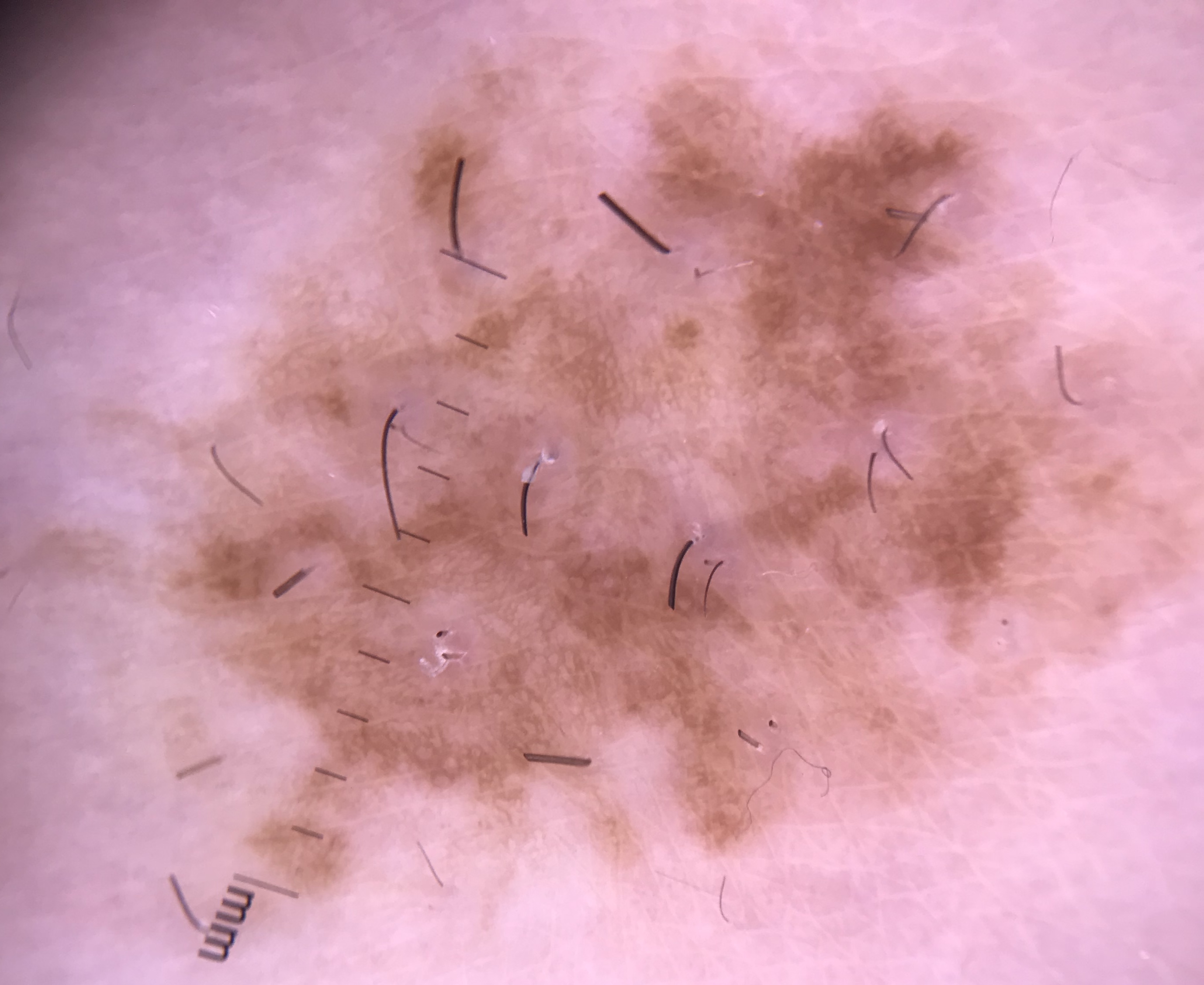- image: dermatoscopy
- category: banal
- diagnostic label: congenital compound nevus (expert consensus)